The condition has been present for less than one week, self-categorized by the patient as a rash, this image was taken at an angle, the arm is involved, the contributor notes itching, the lesion is described as fluid-filled and raised or bumpy: 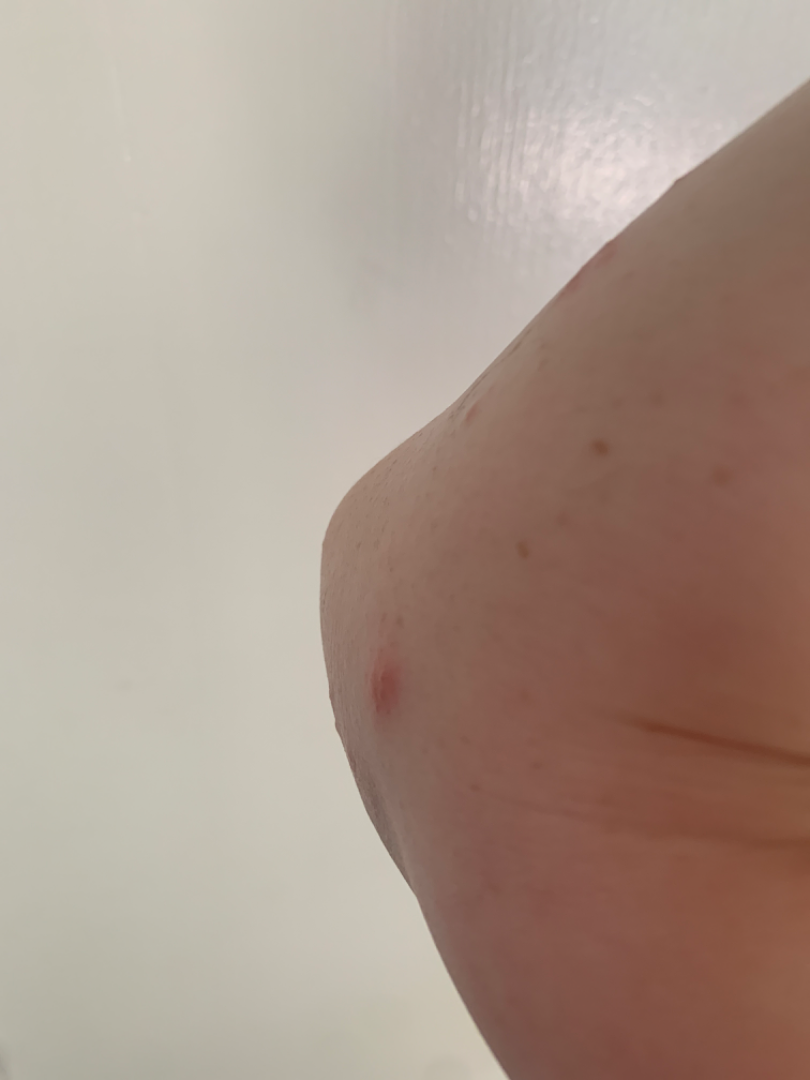Most consistent with Insect Bite.